A male subject in their early 70s; a clinical photograph of a skin lesion; recorded as skin type II: 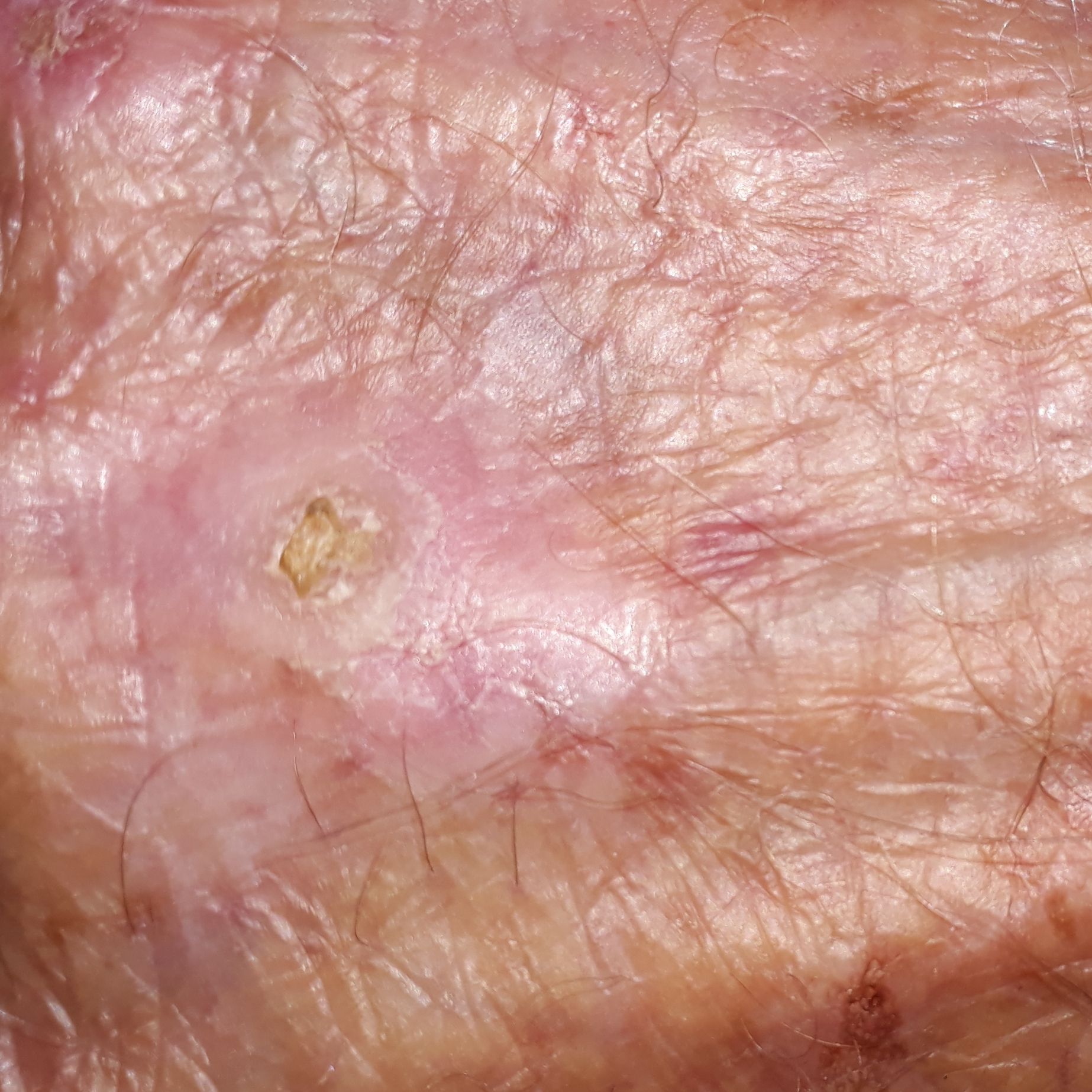  lesion_location: a hand
  symptoms:
    present:
      - elevation
      - growth
  diagnosis:
    name: actinic keratosis
    code: ACK
    malignancy: indeterminate
    confirmation: clinical consensus